The photograph was taken at a distance; located on the leg; the patient also reports fatigue, joint pain and fever; the contributor notes the lesion is raised or bumpy; female subject, age 40–49; symptoms reported: pain:
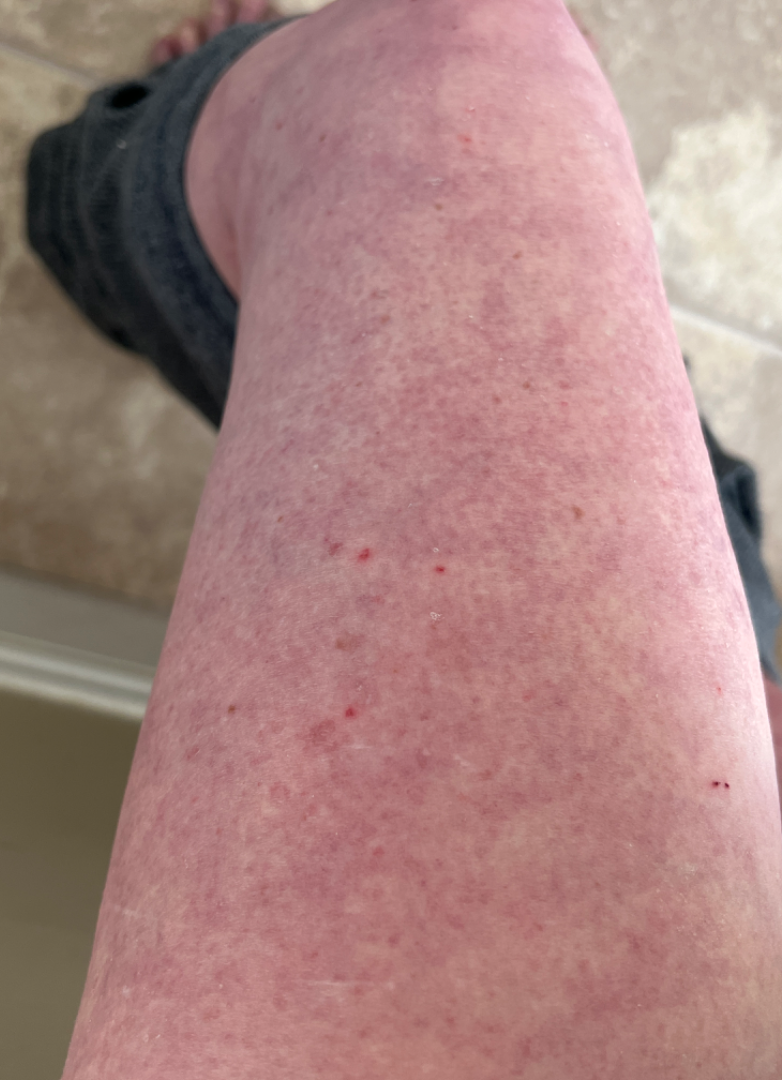Diagnostic features were not clearly distinguishable in this photograph.